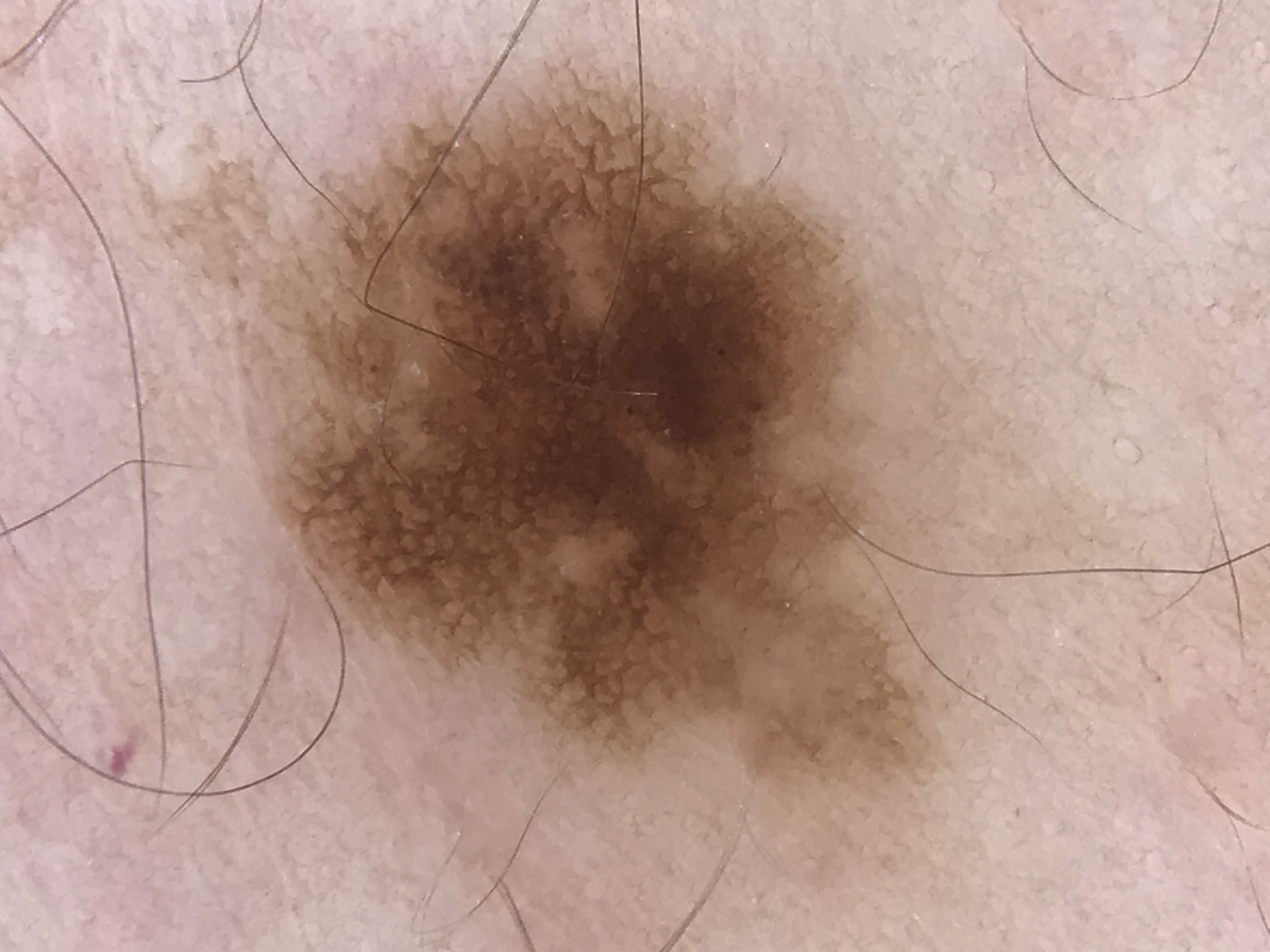A dermoscopic photograph of a skin lesion.
The diagnosis was a benign lesion — a dysplastic junctional nevus.